A clinical photograph of a skin lesion. Recorded as Fitzpatrick skin type II. A female subject in their mid-50s. The chart notes alcohol use and pesticide exposure.
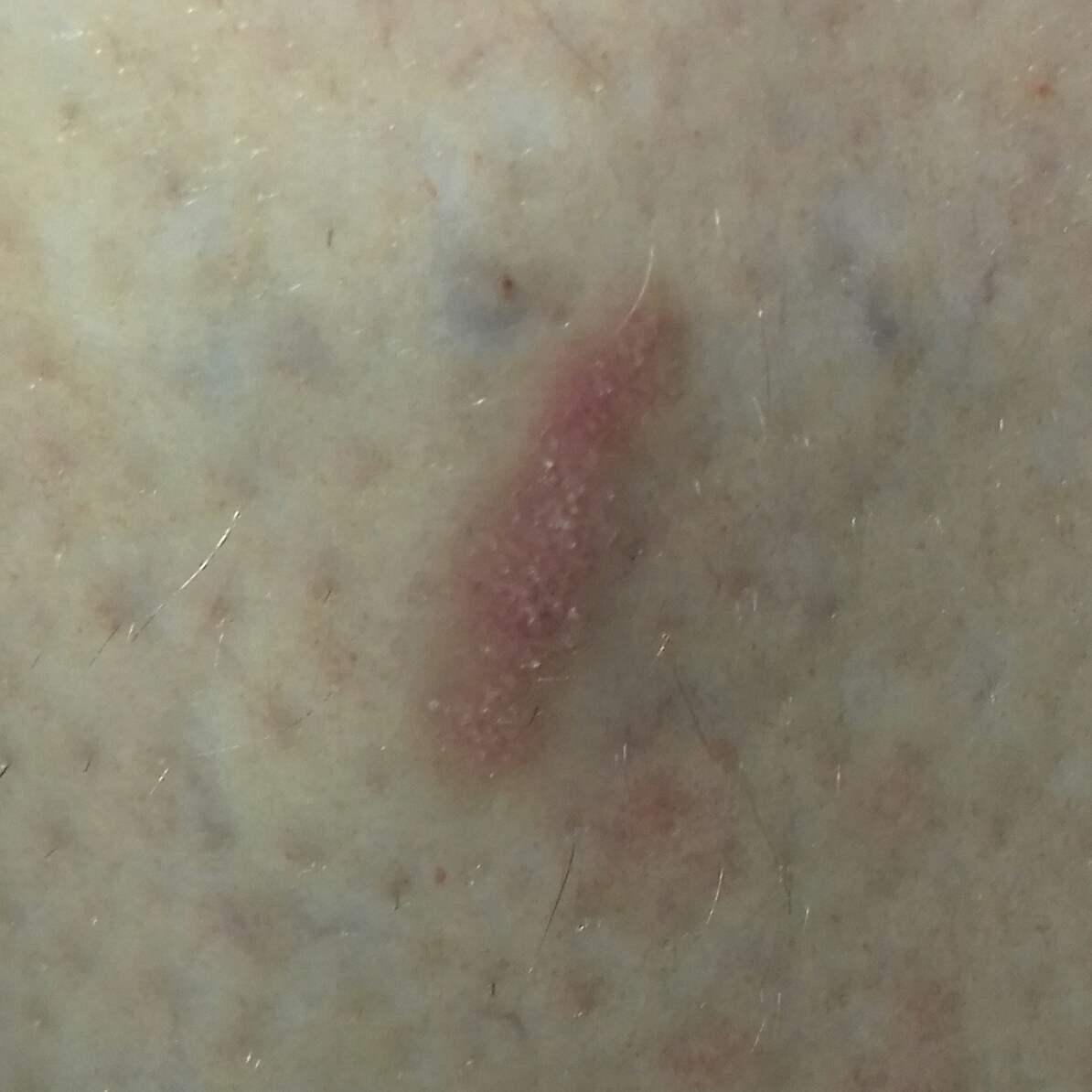location: a thigh, size: 16x5 mm, patient-reported symptoms: no growth, pathology: actinic keratosis (biopsy-proven).